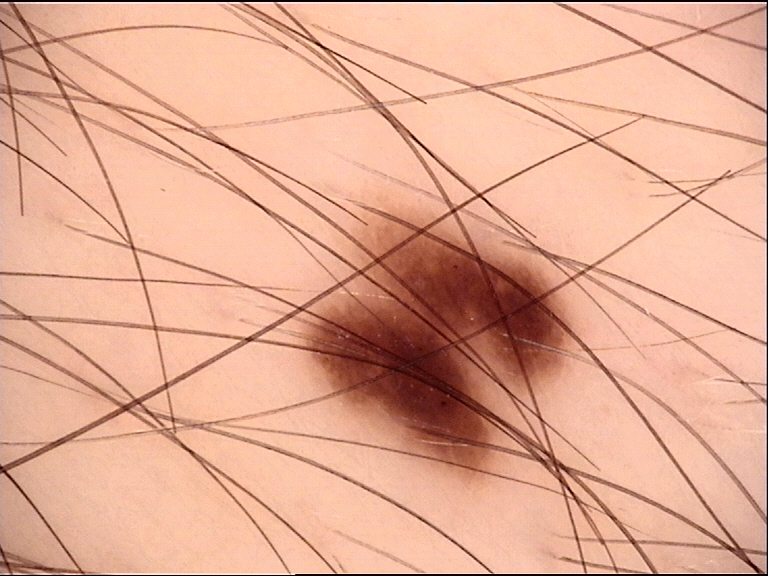{
  "diagnosis": {
    "name": "dysplastic junctional nevus",
    "code": "jd",
    "malignancy": "benign",
    "super_class": "melanocytic",
    "confirmation": "expert consensus"
  }
}